A skin lesion imaged with a dermatoscope: 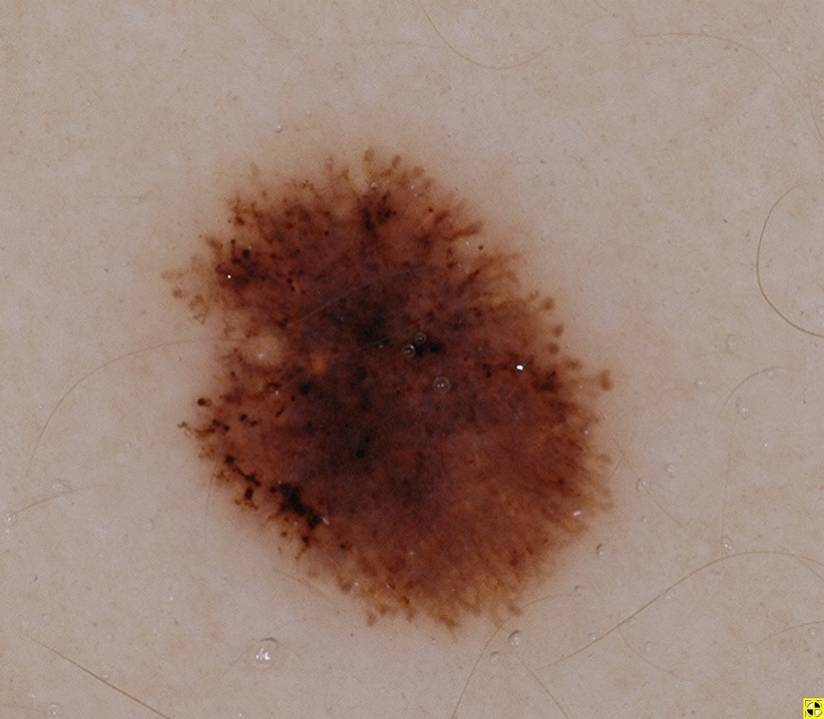In (x1, y1, x2, y2) order, the lesion spans box(169, 146, 612, 629).
On dermoscopy, the lesion shows globules, streaks, and pigment network.
Expert review diagnosed this as a melanocytic nevus.